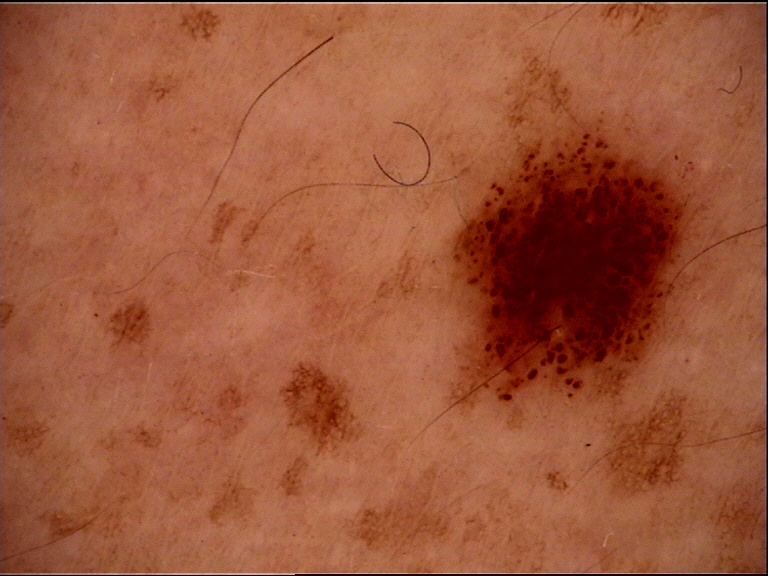Case: A dermatoscopic image of a skin lesion. Conclusion: The diagnosis was a banal lesion — a compound nevus.